A dermoscopic photograph of a skin lesion.
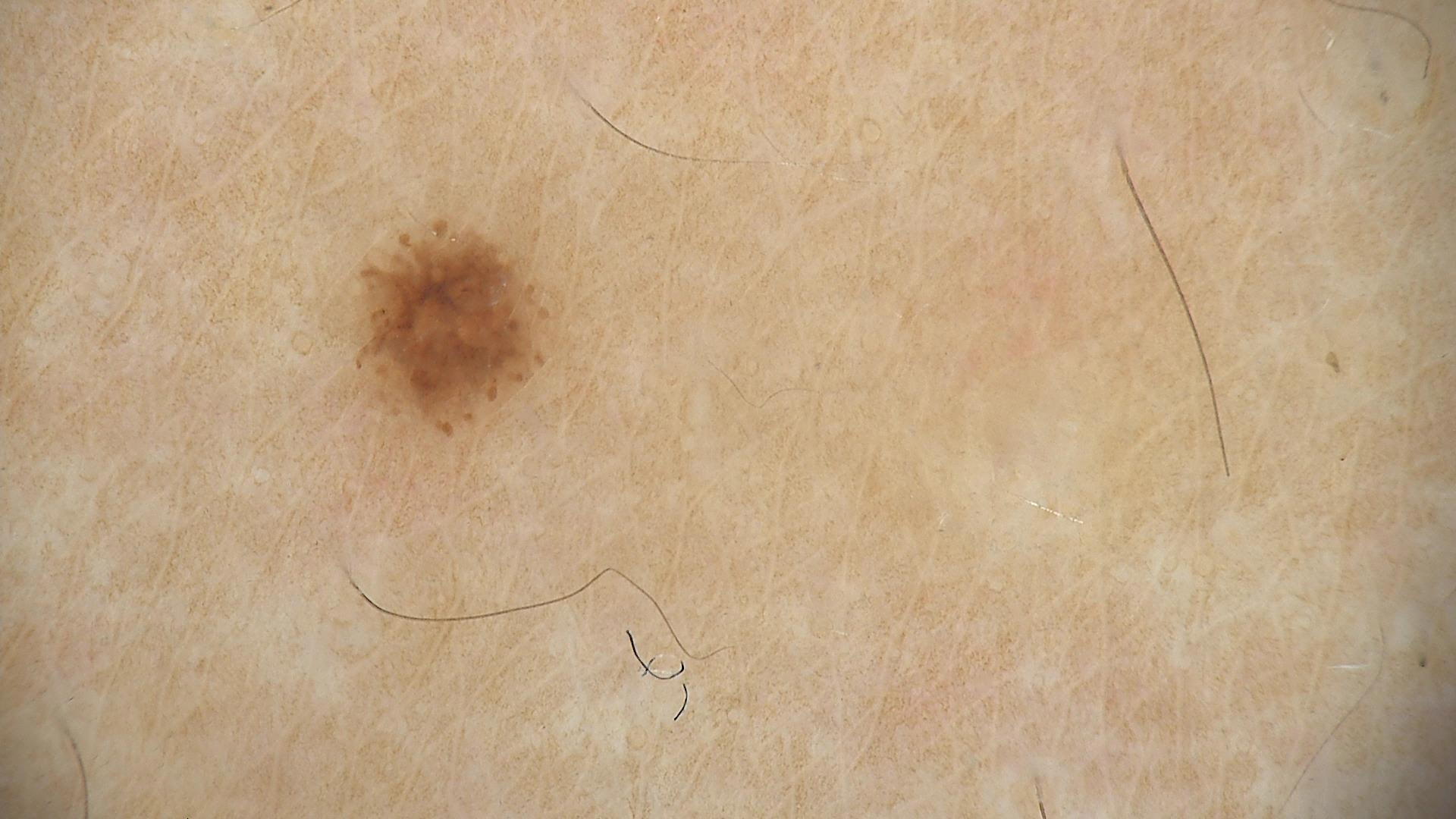Classified as a dysplastic junctional nevus.